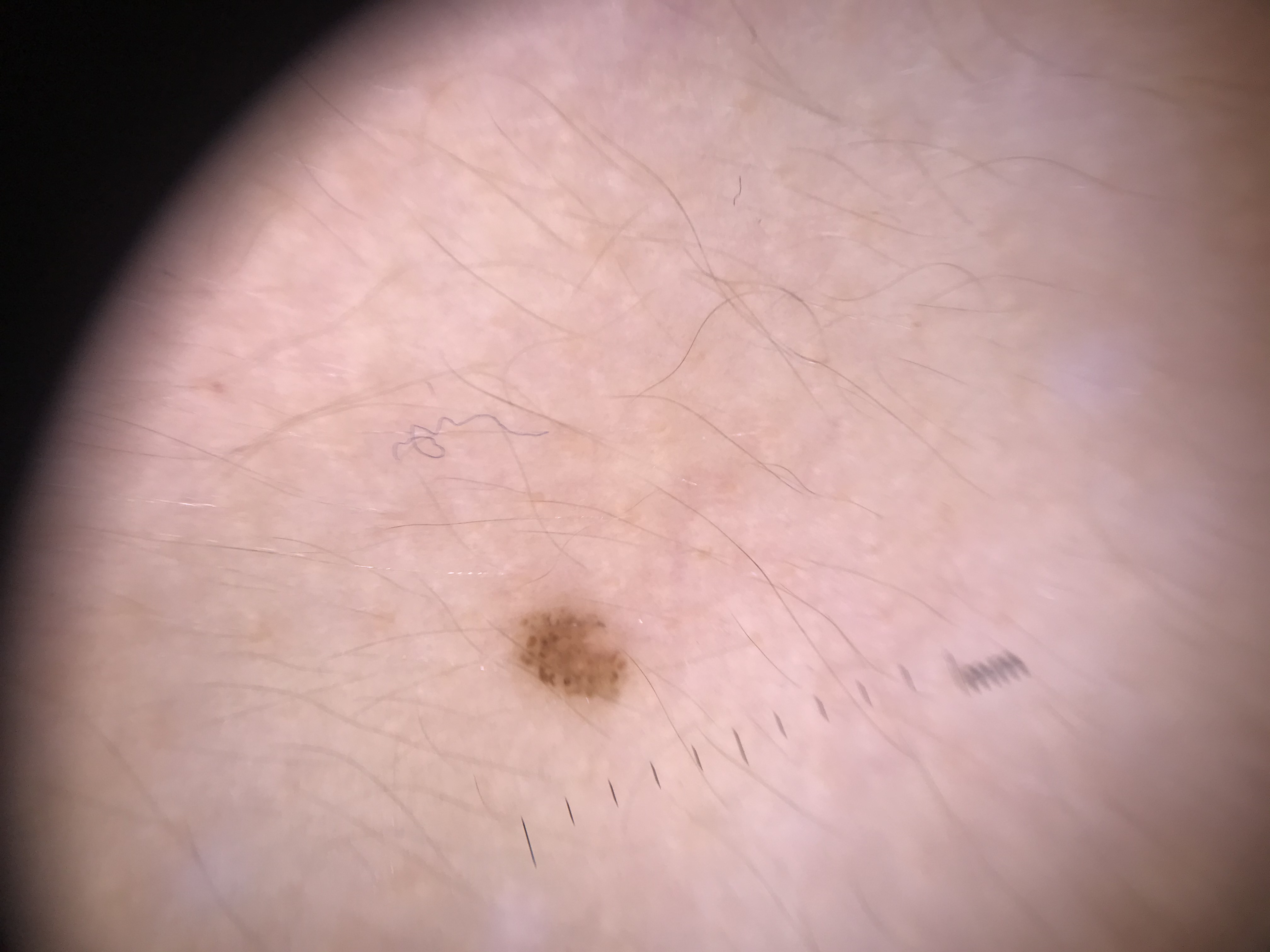class — junctional nevus (expert consensus)